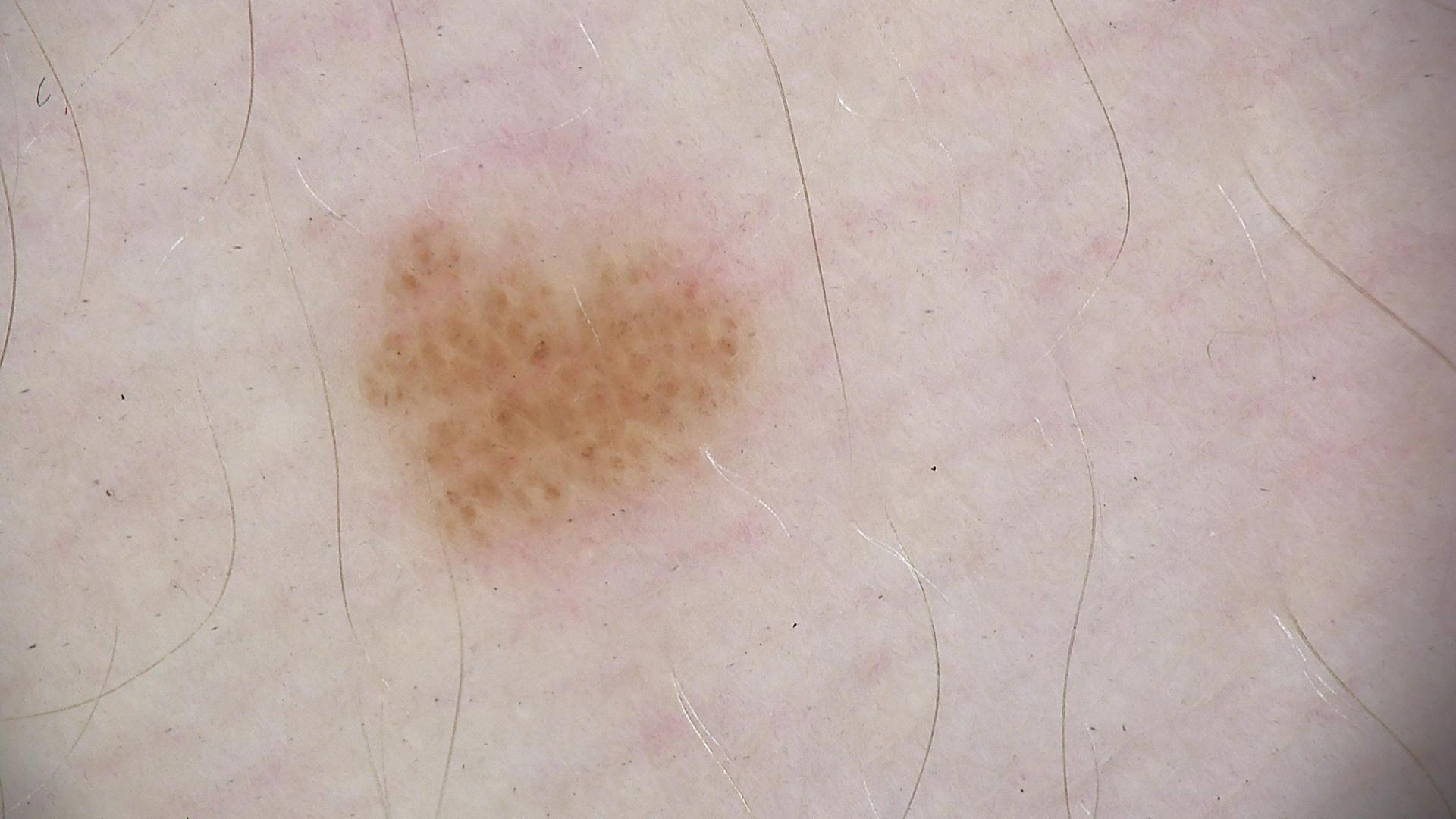<lesion>
<image>dermatoscopy</image>
<diagnosis>
<name>junctional nevus</name>
<code>jb</code>
<malignancy>benign</malignancy>
<super_class>melanocytic</super_class>
<confirmation>expert consensus</confirmation>
</diagnosis>
</lesion>